The patient is 70–79, male · texture is reported as flat · self-categorized by the patient as a rash · reported duration is about one day · symptoms reported: bothersome appearance · a close-up photograph.
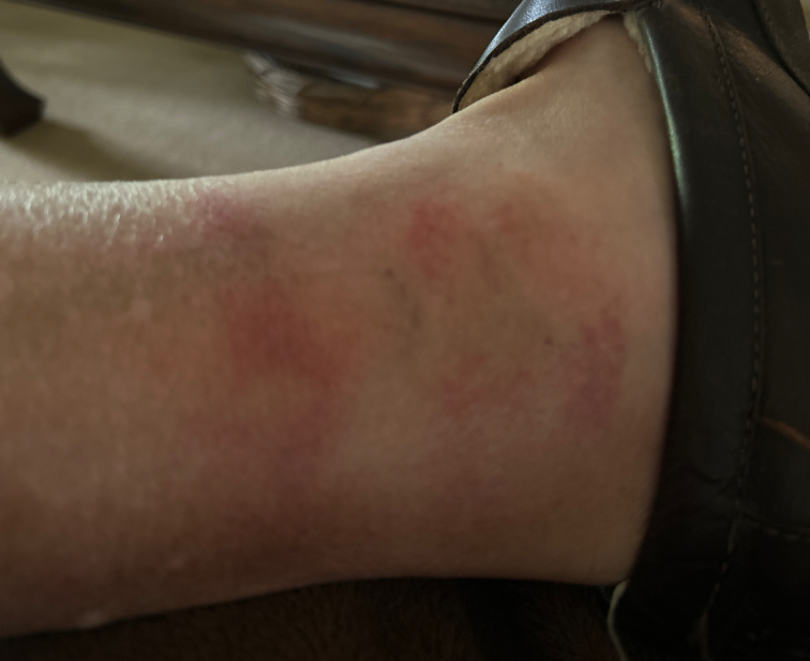clinical impression = Eczema, Stasis Dermatitis and Allergic Contact Dermatitis were considered with similar weight